A skin lesion imaged with a dermatoscope — 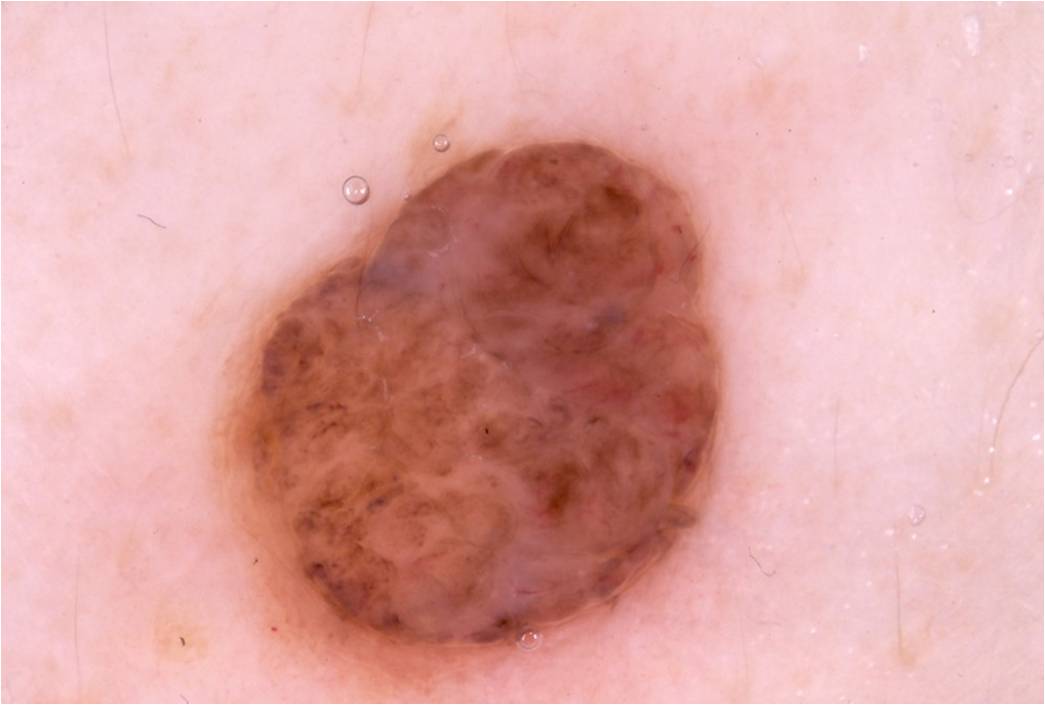With coordinates (x1, y1, x2, y2), lesion location: (222, 138, 721, 681). The dermoscopic pattern shows no globules, negative network, milia-like cysts, pigment network, or streaks. A mid-sized lesion within the field. Clinically diagnosed as a melanocytic nevus.